A male subject, in their mid- to late 70s; a dermoscopic close-up of a skin lesion.
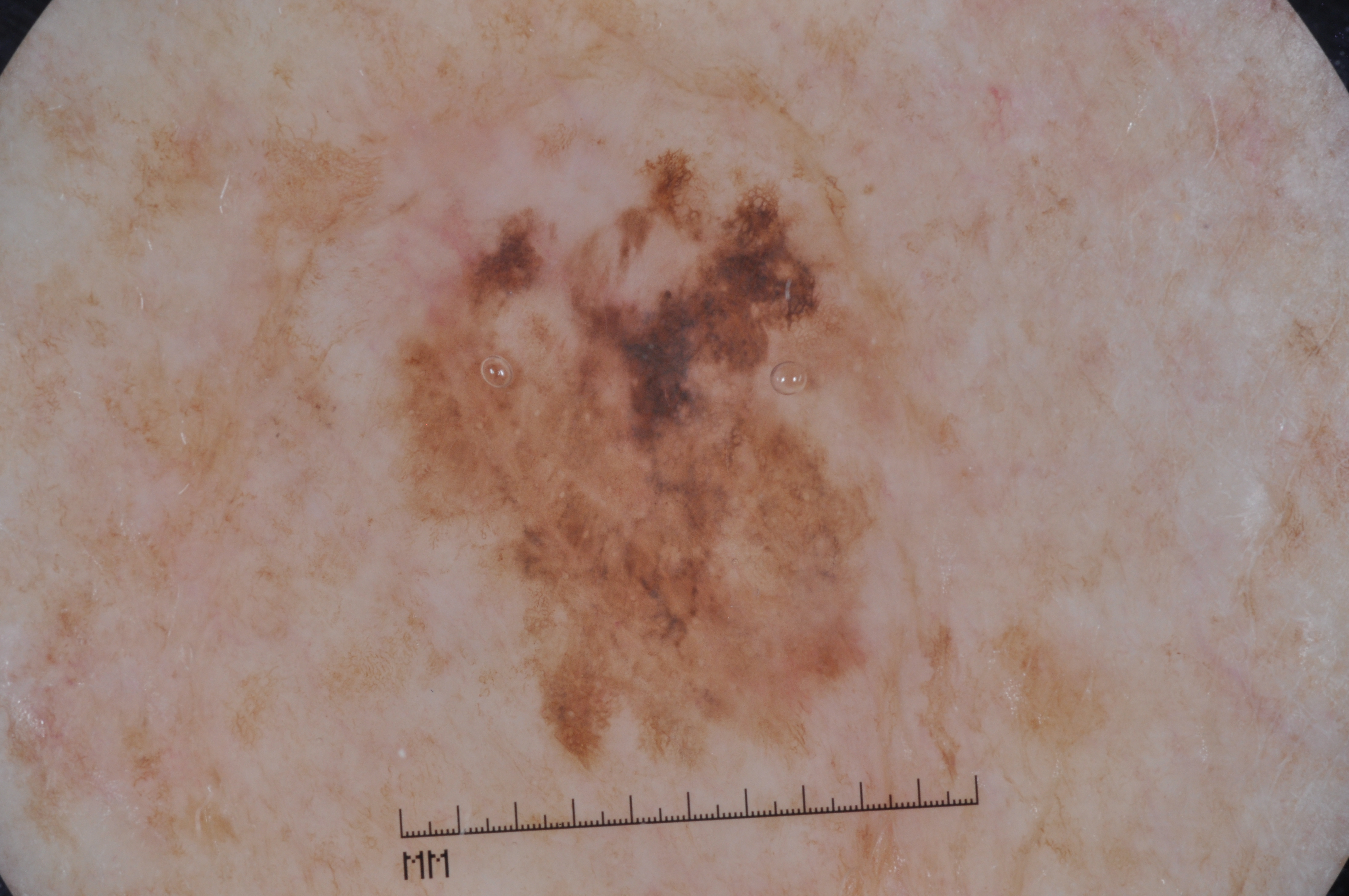Lesion location: 390, 175, 916, 749.
Dermoscopically, the lesion shows pigment network and milia-like cysts; no negative network or streaks.
Confirmed on histopathology as a melanoma, a skin cancer.